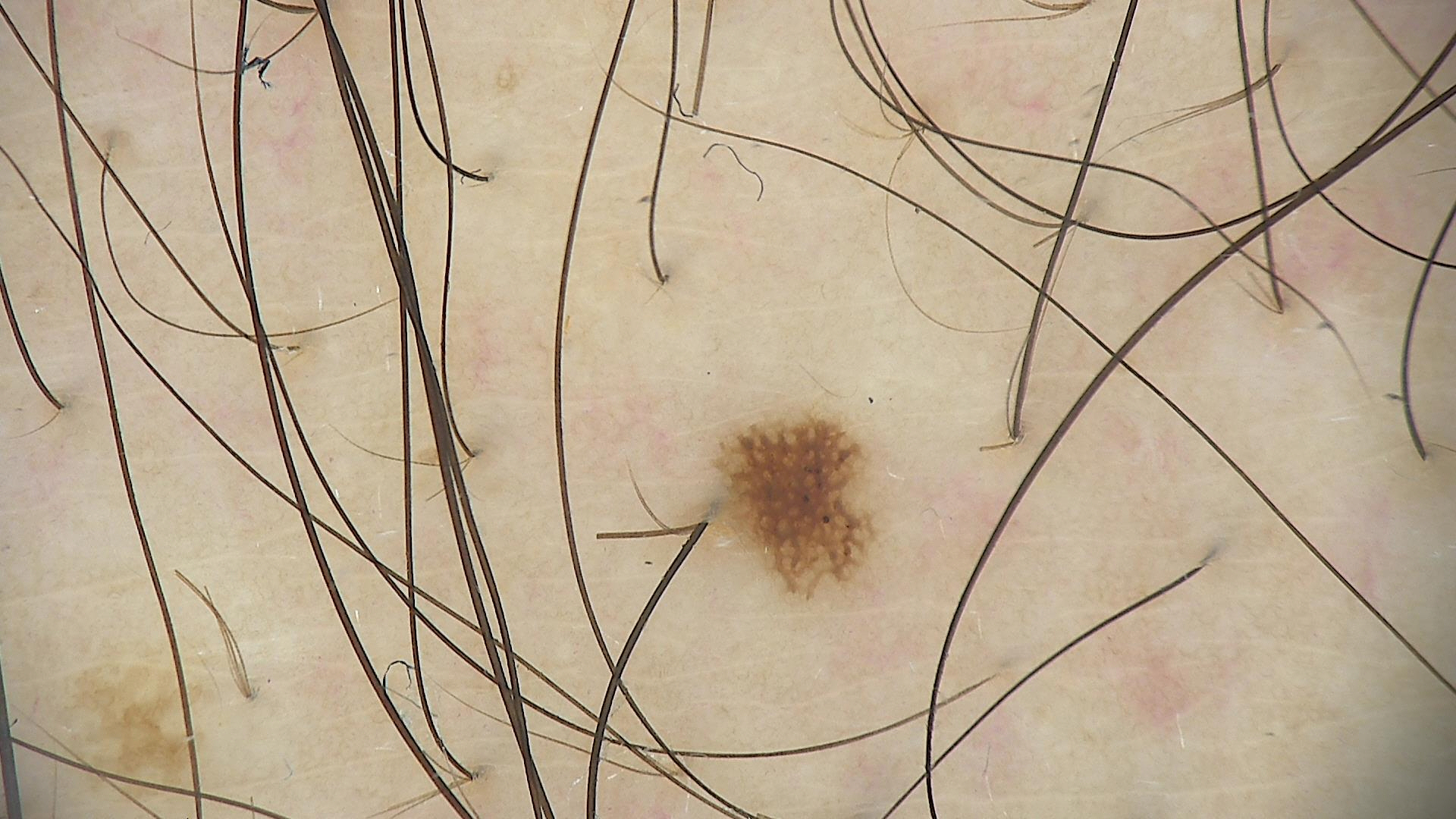image type=dermoscopy; diagnostic label=dysplastic junctional nevus (expert consensus).